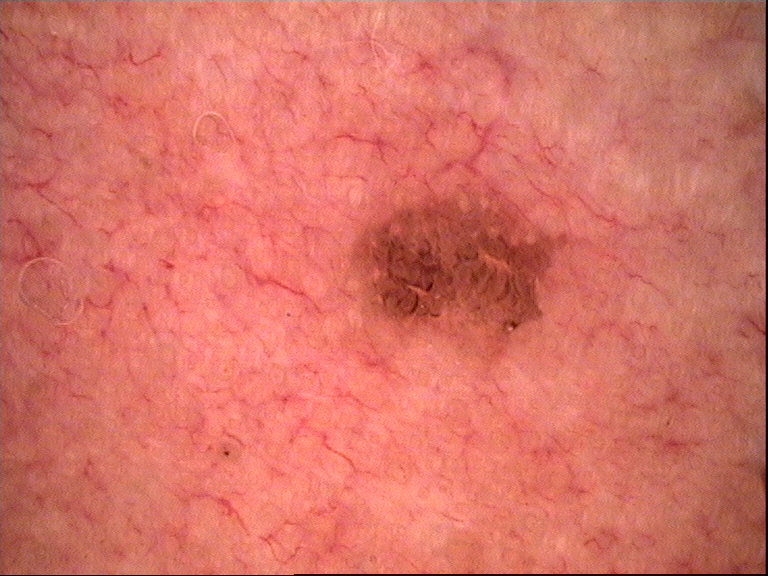A dermoscopic close-up of a skin lesion.
Classified as a benign lesion — a seborrheic keratosis.